A dermoscopic image of a skin lesion.
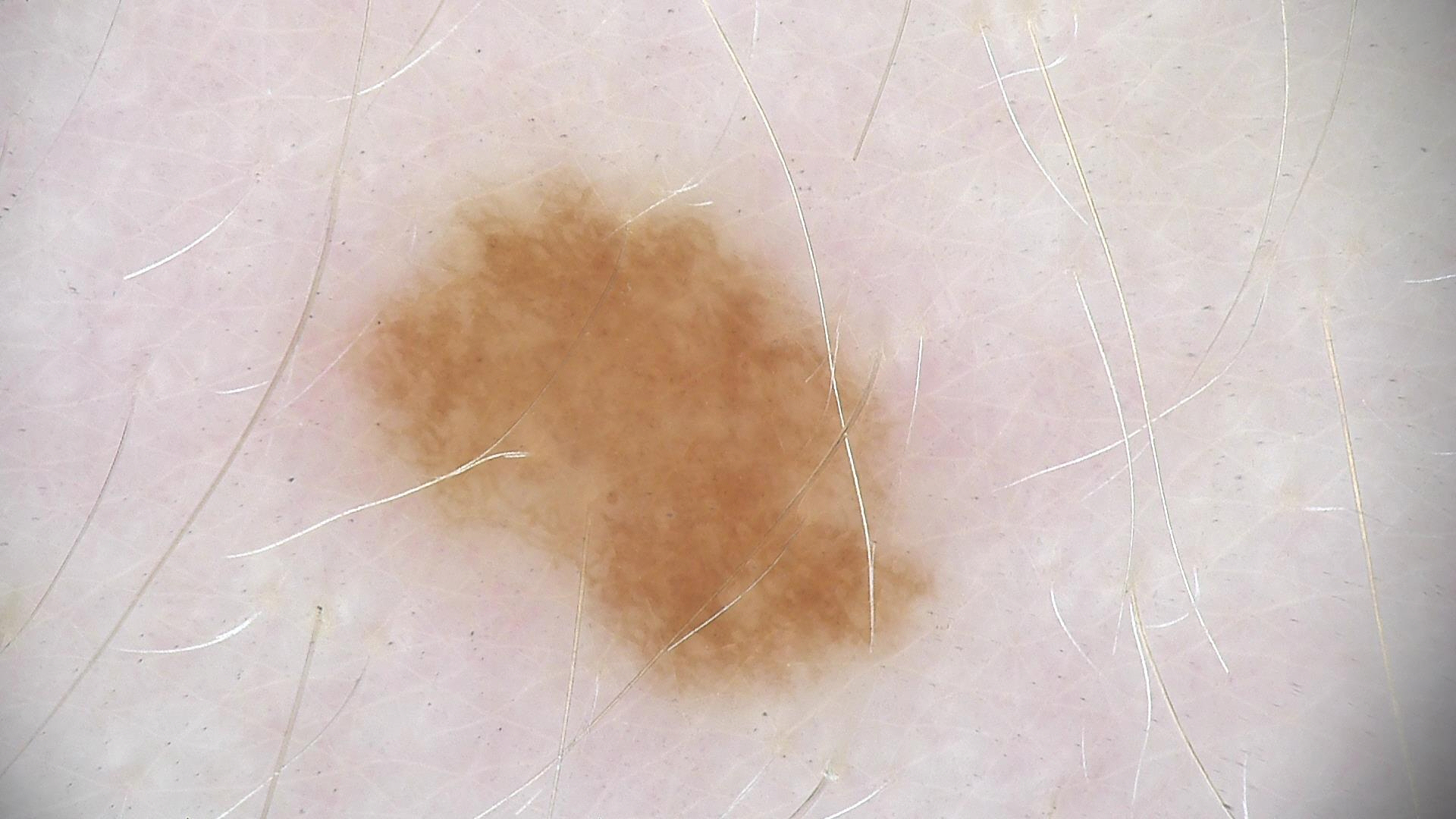Conclusion:
Classified as a benign lesion — a dysplastic junctional nevus.